The lesion is associated with itching · FST II; lay reviewers estimated 3 on the Monk skin tone scale · an image taken at an angle · the lesion involves the leg and front of the torso.
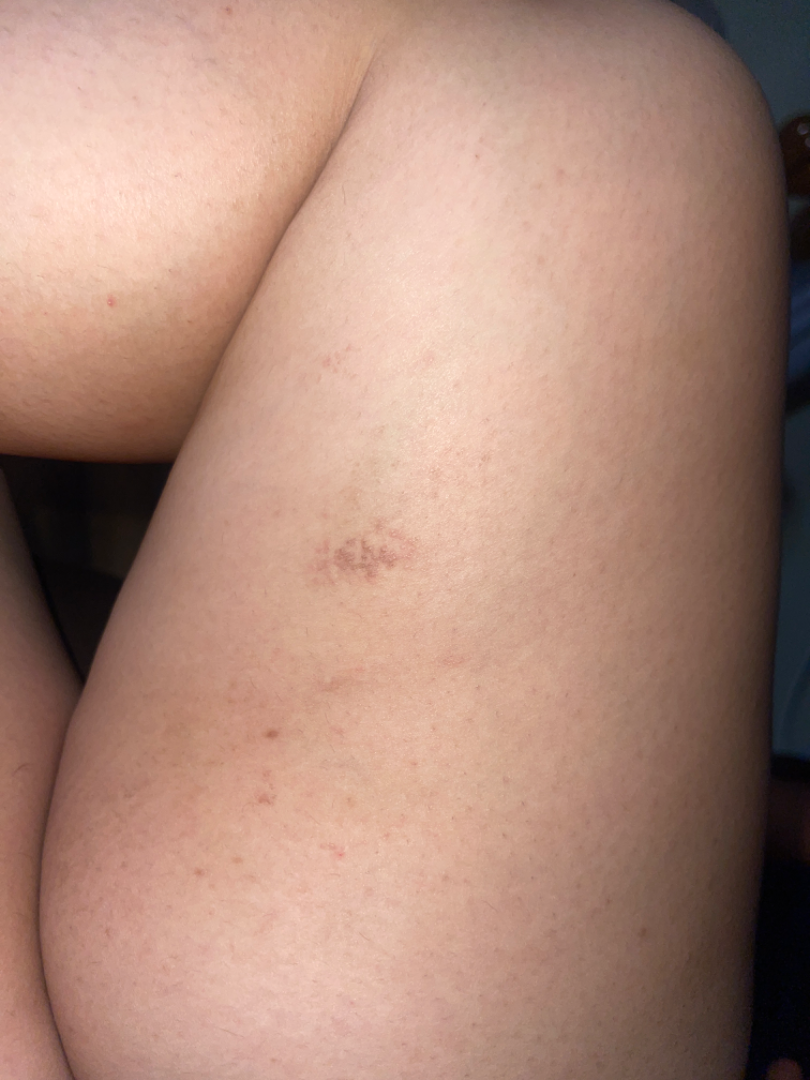Findings:
– diagnostic considerations: Eczema (favored); Epidermal nevus (considered); Milia (considered)